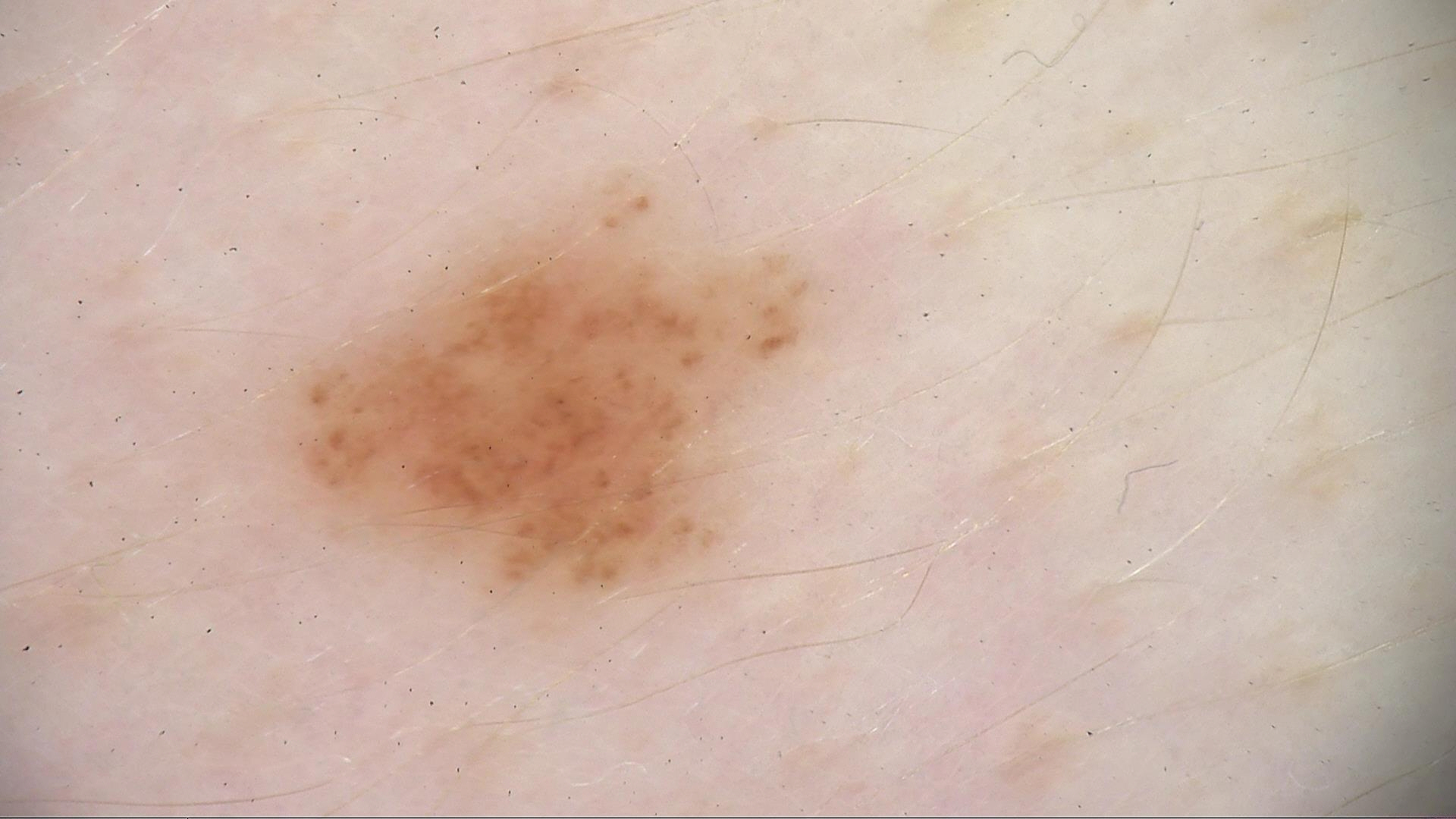{
  "diagnosis": {
    "name": "dysplastic junctional nevus",
    "code": "jd",
    "malignancy": "benign",
    "super_class": "melanocytic",
    "confirmation": "expert consensus"
  }
}